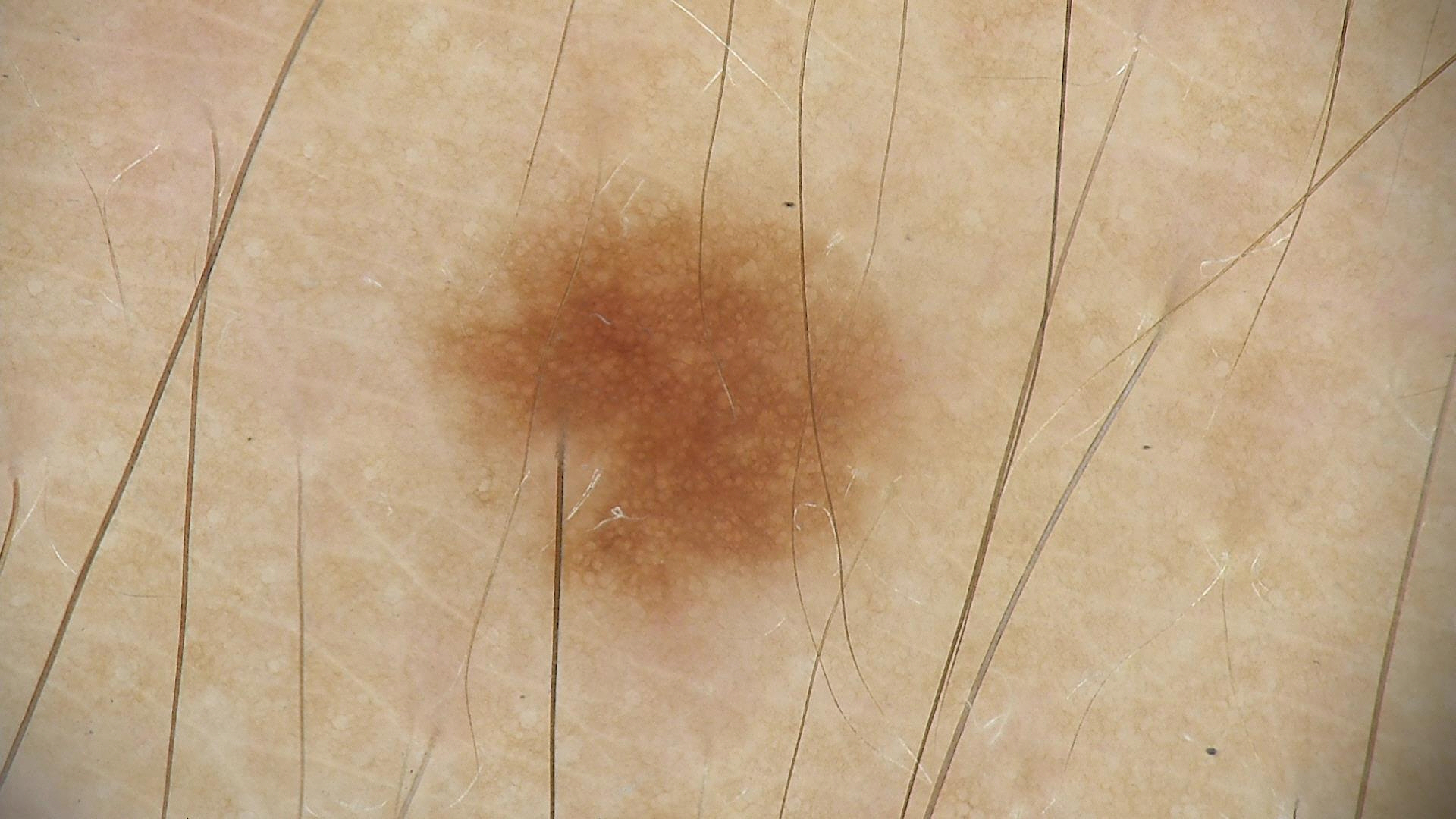Conclusion: Labeled as a dysplastic junctional nevus.